This is a close-up image, located on the leg, the contributor is a male aged 40–49.
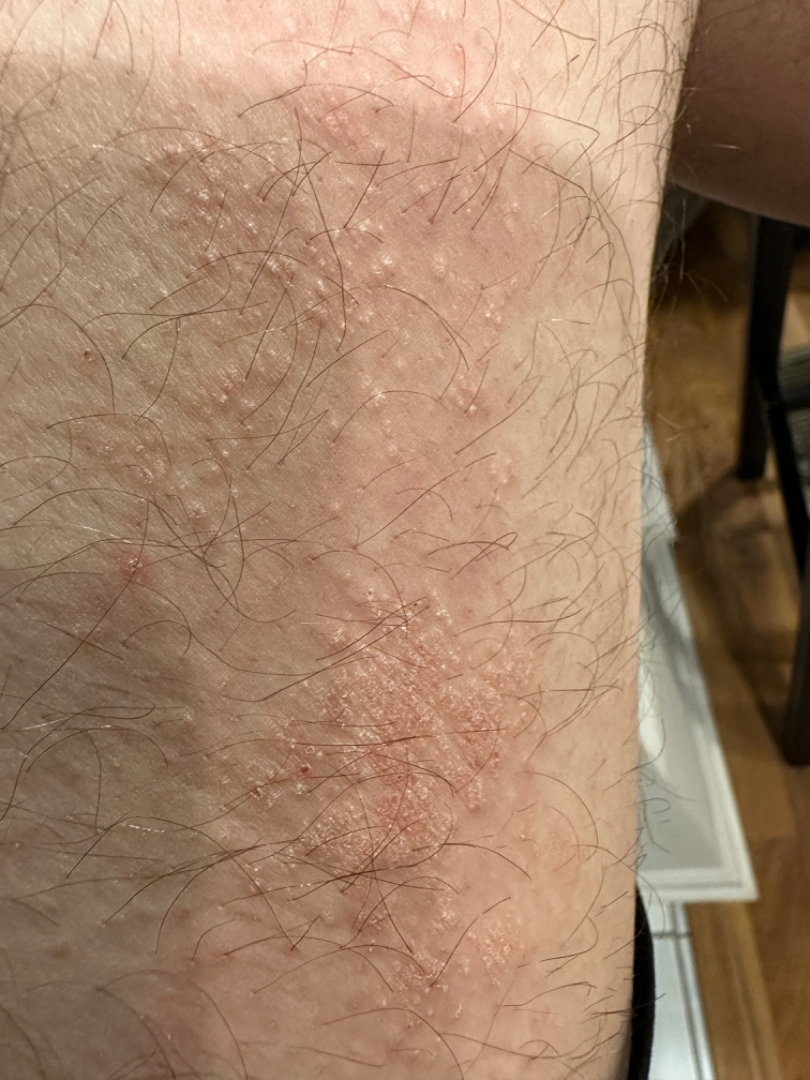other reported symptoms = none reported
patient's own categorization = a rash
onset = less than one week
described texture = raised or bumpy and rough or flaky
assessment = Eczema (most likely); Acute and chronic dermatitis (considered); Tinea (remote)